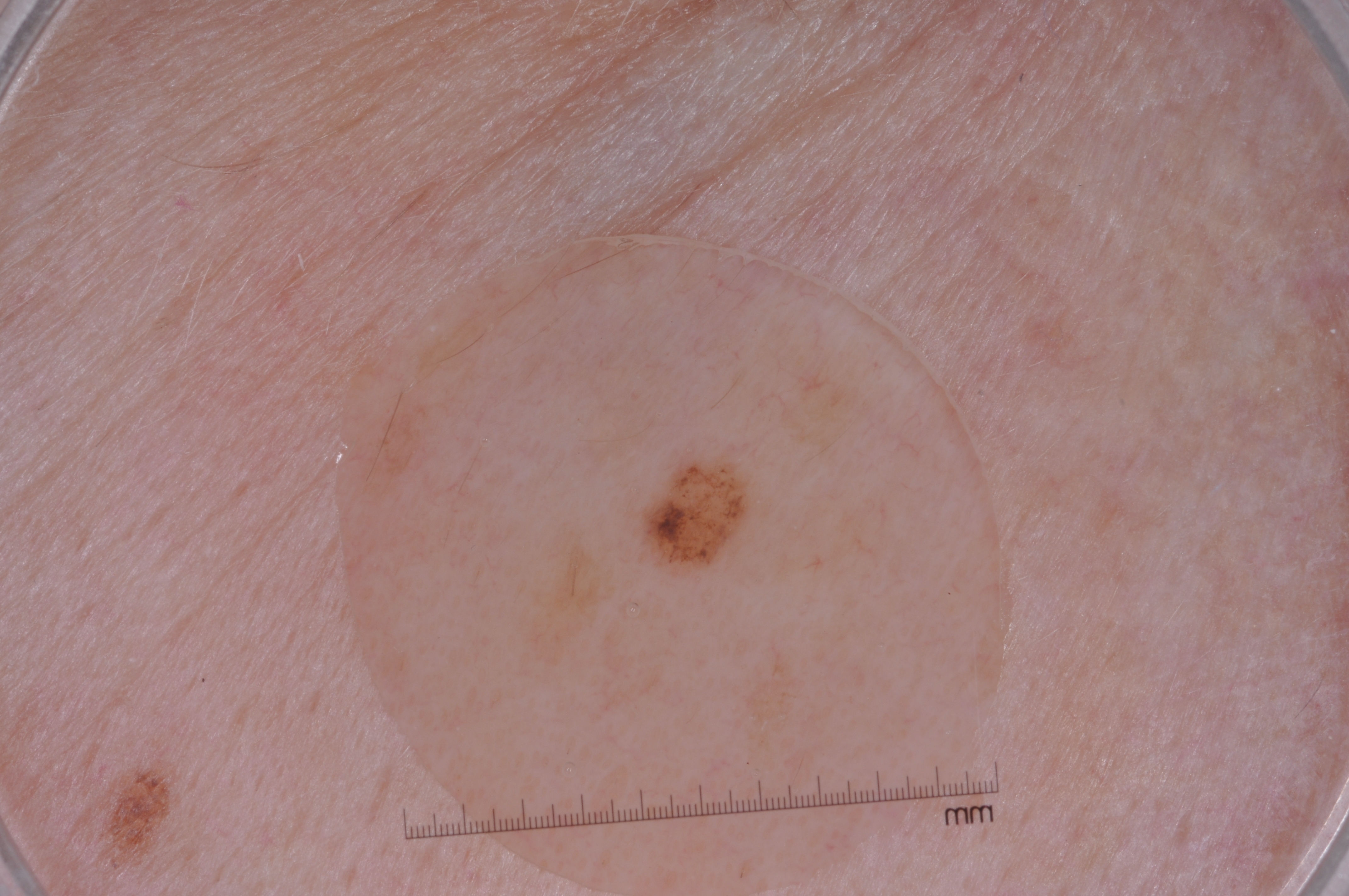The subject is a female in their 50s.
A dermoscopic close-up of a skin lesion.
The lesion is small relative to the field of view.
Dermoscopy demonstrates pigment network, with no streaks, negative network, or milia-like cysts.
The lesion spans bbox(624, 452, 758, 577).
Clinically diagnosed as a melanocytic nevus, a benign lesion.